The patient considered this a rash; the arm is involved; the contributor is female; the photograph is a close-up of the affected area; symptoms reported: enlargement, bothersome appearance and itching — 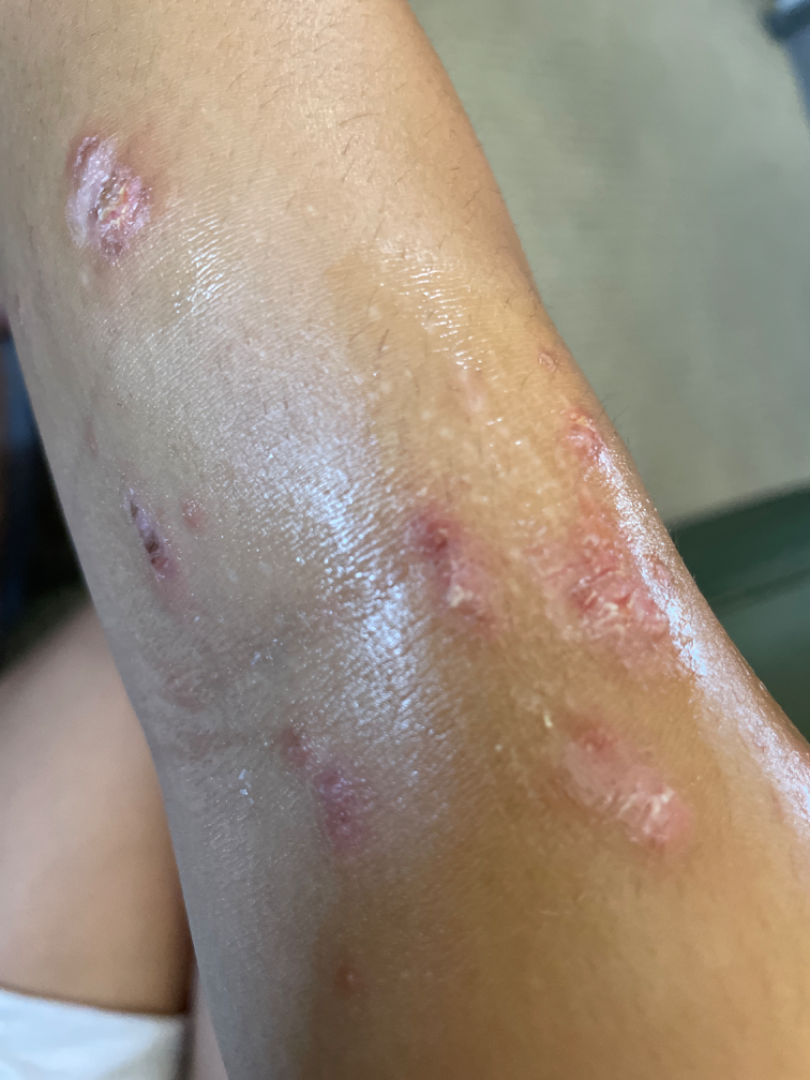The reviewing dermatologists' impression was: the leading consideration is Lichen Simplex Chronicus; possibly Inflicted skin lesions; also on the differential is Eczema; less likely is Infected eczema; less probable is Abrasion of wrist.